The subject is a female aged 30–39. No constitutional symptoms were reported. Skin tone: Fitzpatrick IV; non-clinician graders estimated MST 2 (US pool) or 4 (India pool). A close-up photograph. The affected area is the top or side of the foot.
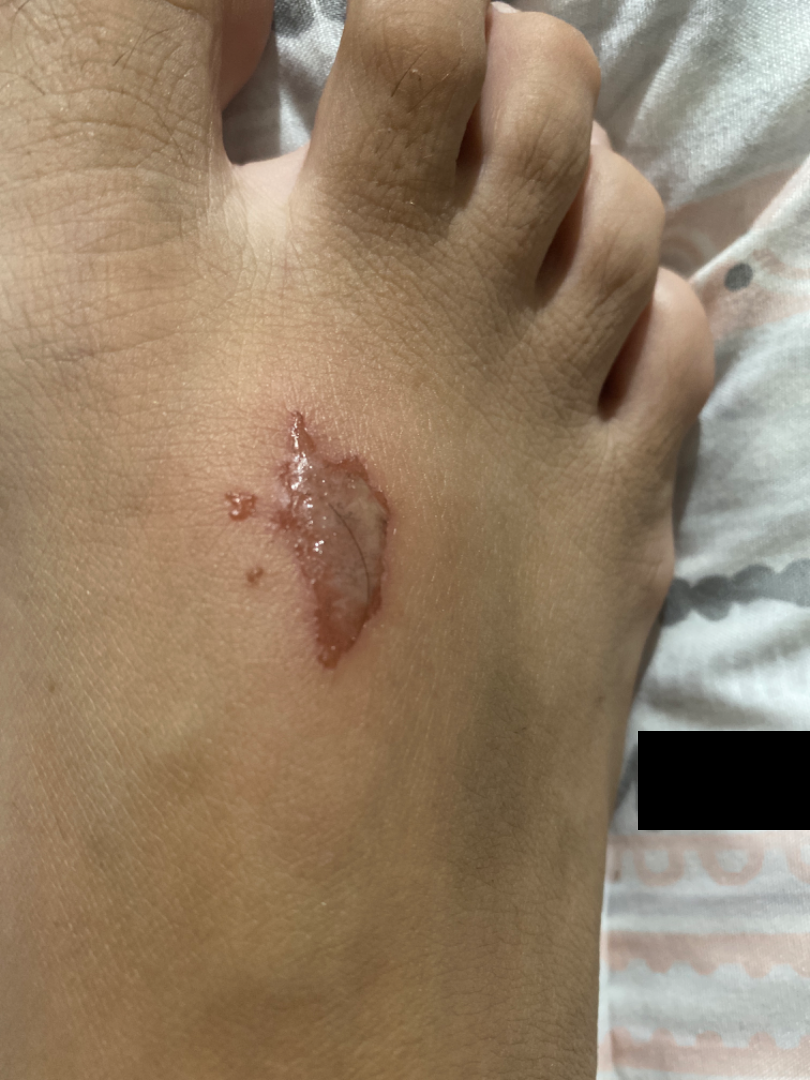Q: What conditions are considered?
A: most consistent with Burn of skin; also consider Skin infection; a remote consideration is Allergic Contact Dermatitis